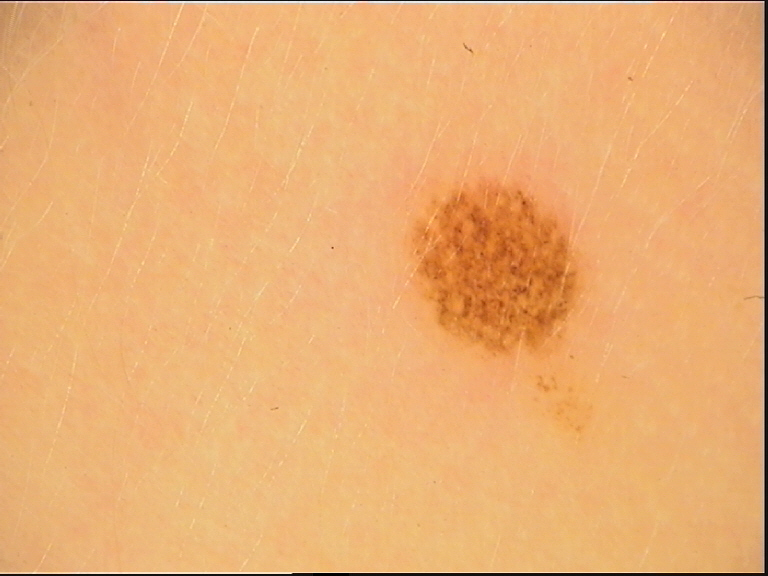{"image": "dermoscopy", "lesion_type": {"main_class": "banal", "pattern": "compound"}, "diagnosis": {"name": "Miescher nevus", "code": "mcb", "malignancy": "benign", "super_class": "melanocytic", "confirmation": "expert consensus"}}